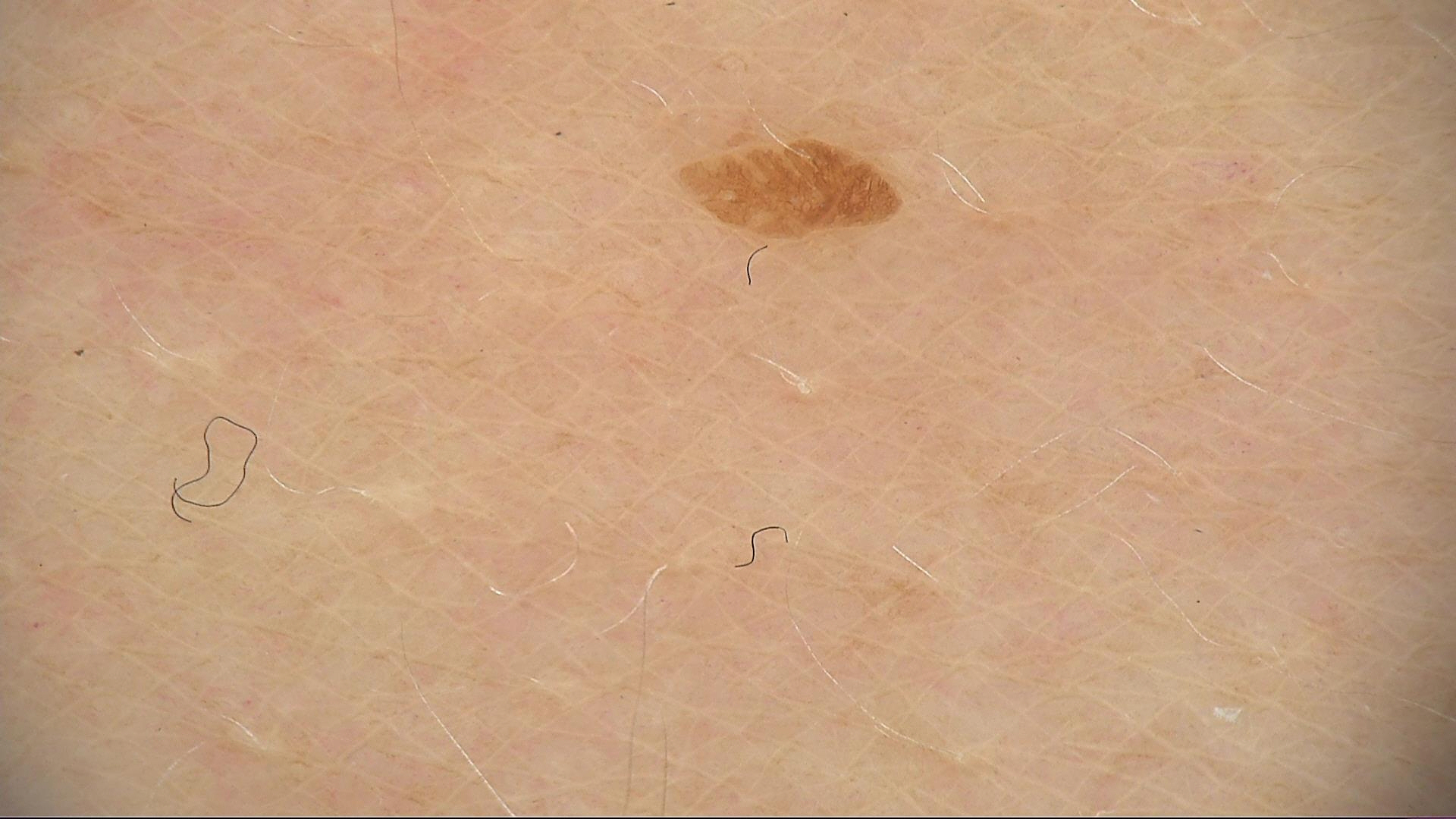Conclusion: The diagnosis was a seborrheic keratosis.